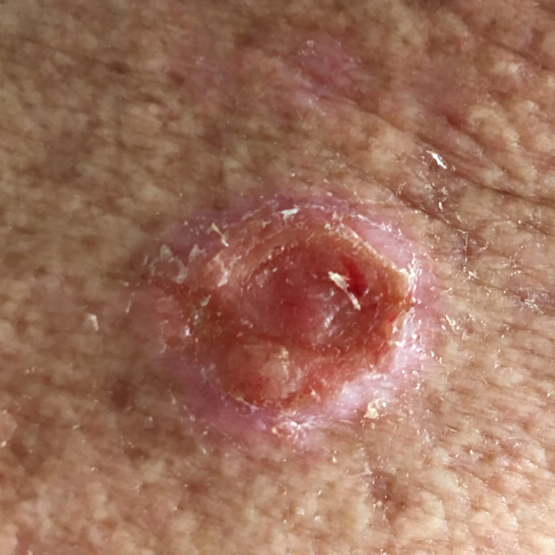Q: What kind of image is this?
A: clinical photograph
Q: Patient demographics?
A: male, age 57
Q: What are the relevant risk factors?
A: pesticide exposure, prior malignancy (patient or family)
Q: What is the anatomic site?
A: the back
Q: How large is the lesion?
A: 23 × 20 mm
Q: What did the workup show?
A: squamous cell carcinoma (biopsy-proven)